The patient notes the lesion is raised or bumpy; self-categorized by the patient as a rash; symptoms reported: itching, bothersome appearance, enlargement and burning; the arm, front of the torso and back of the torso are involved; the contributor is a female aged 18–29; the photograph is a close-up of the affected area; the patient notes associated chills; reported duration is about one day — 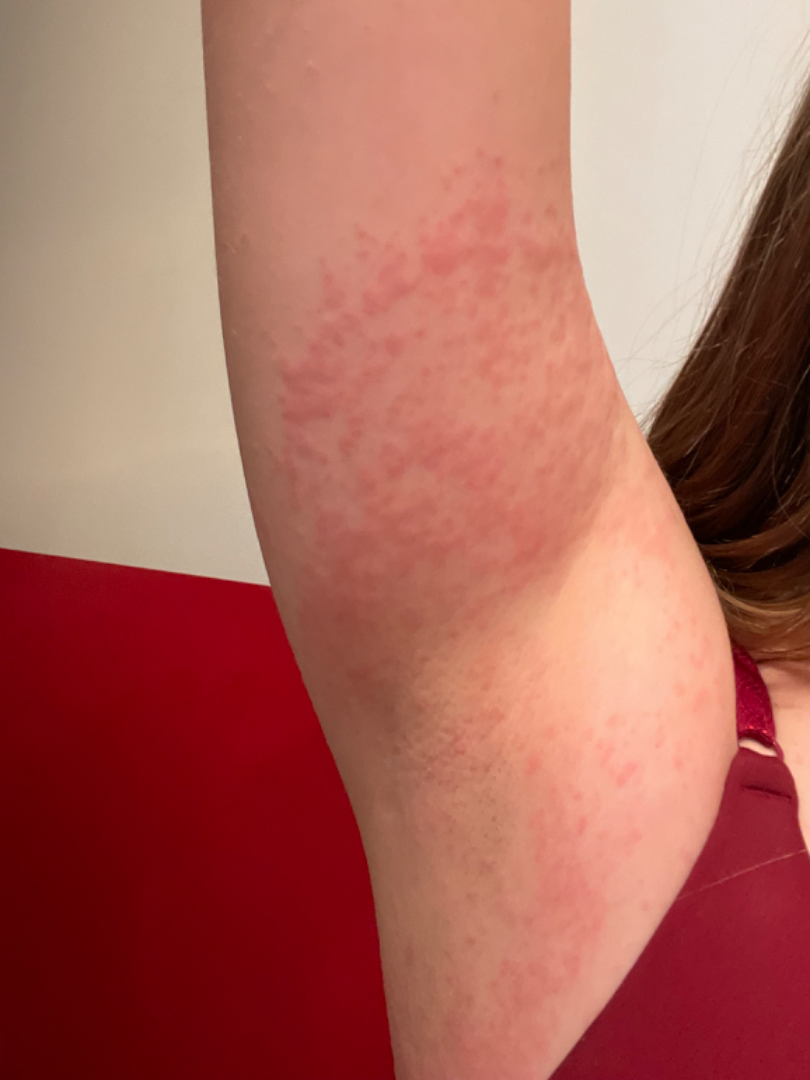Case summary:
* clinical impression — most consistent with Allergic Contact Dermatitis; also raised was Irritant Contact Dermatitis